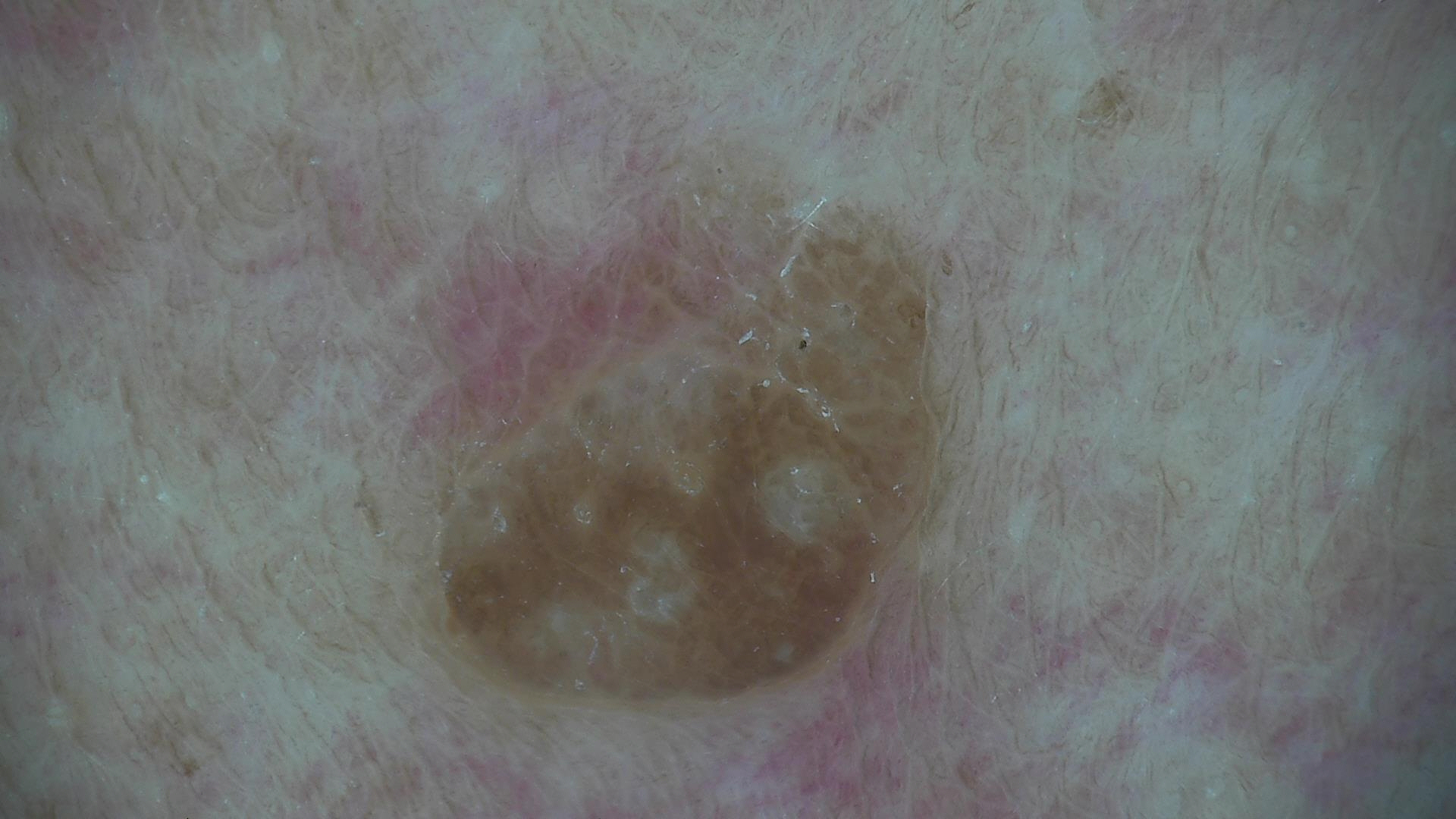The architecture is that of a keratinocytic lesion. Diagnosed as a seborrheic keratosis.